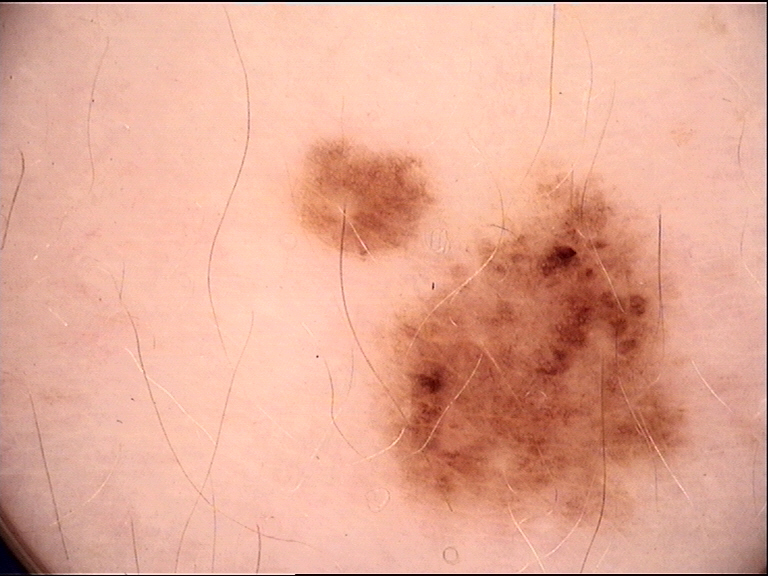imaging — dermoscopy | assessment — dysplastic junctional nevus (expert consensus).